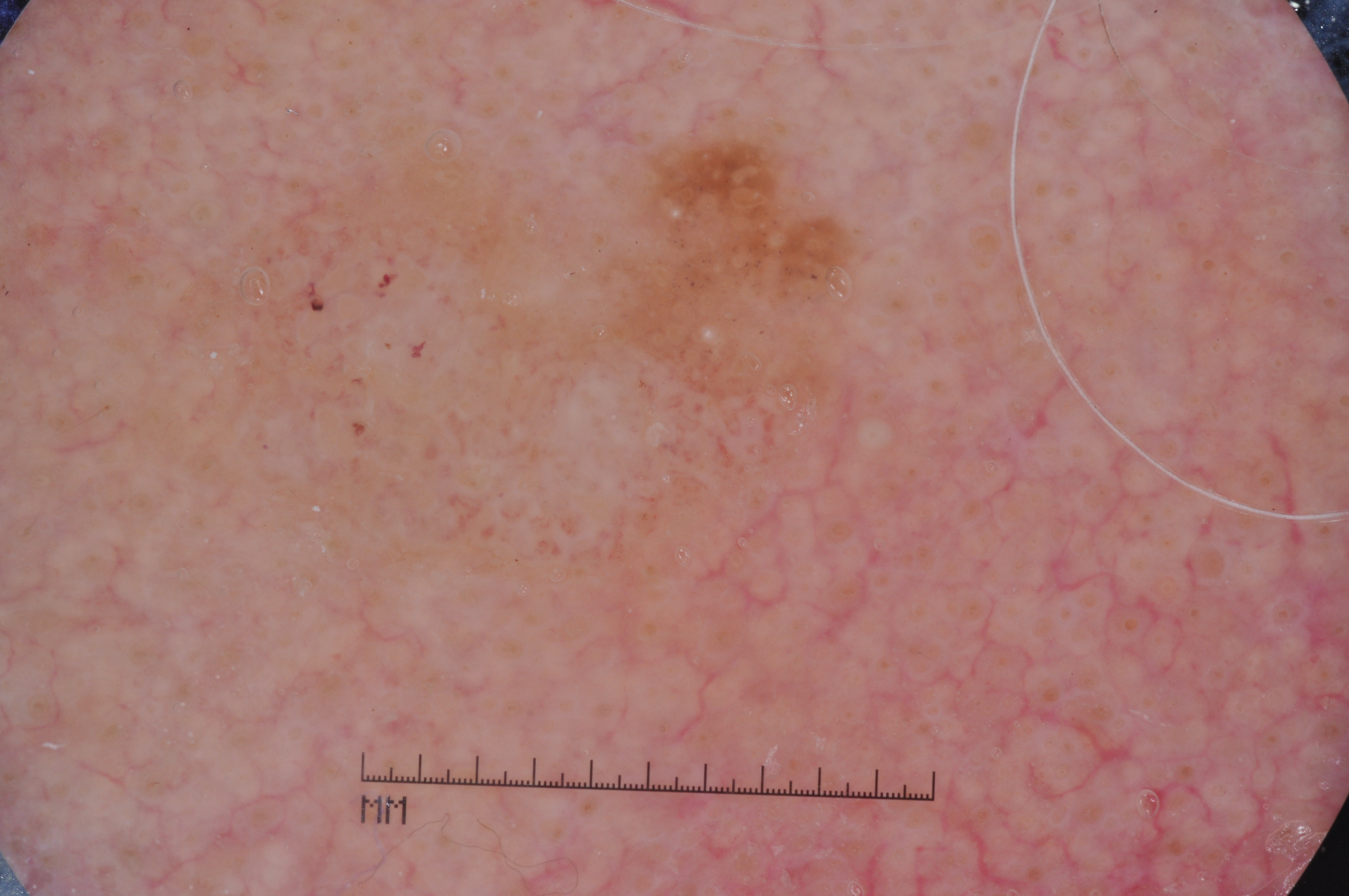Q: What are the patient's age and sex?
A: male, aged 78-82
Q: How was this image acquired?
A: dermatoscopic image of a skin lesion
Q: What dermoscopic features are present?
A: milia-like cysts; absent: pigment network, streaks, and negative network
Q: Lesion extent?
A: moderate
Q: What is the lesion's bounding box?
A: <bbox>103, 83, 937, 648</bbox>
Q: What did the assessment conclude?
A: a seborrheic keratosis, a benign skin lesion